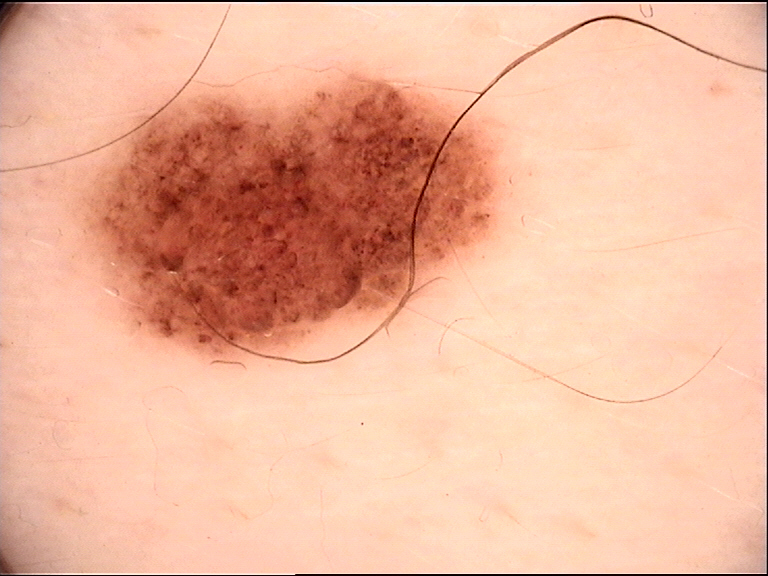image type — dermoscopy; diagnosis — dysplastic junctional nevus (expert consensus).